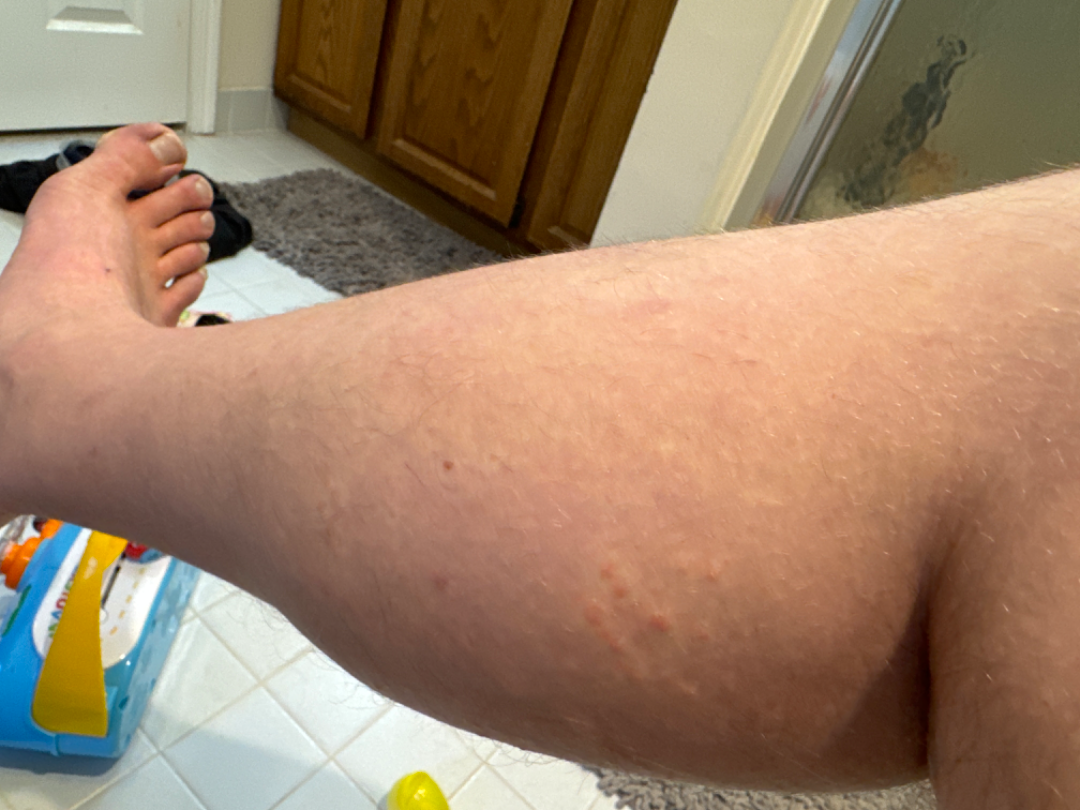{
  "duration": "less than one week",
  "shot_type": "at a distance",
  "patient": "male, age 30–39",
  "symptoms": "itching",
  "skin_tone": {
    "fitzpatrick": "II"
  },
  "texture": "raised or bumpy",
  "body_site": "leg",
  "patient_category": "a rash",
  "differential": {
    "leading": [
      "Insect Bite"
    ],
    "considered": [
      "Hypersensitivity"
    ]
  }
}